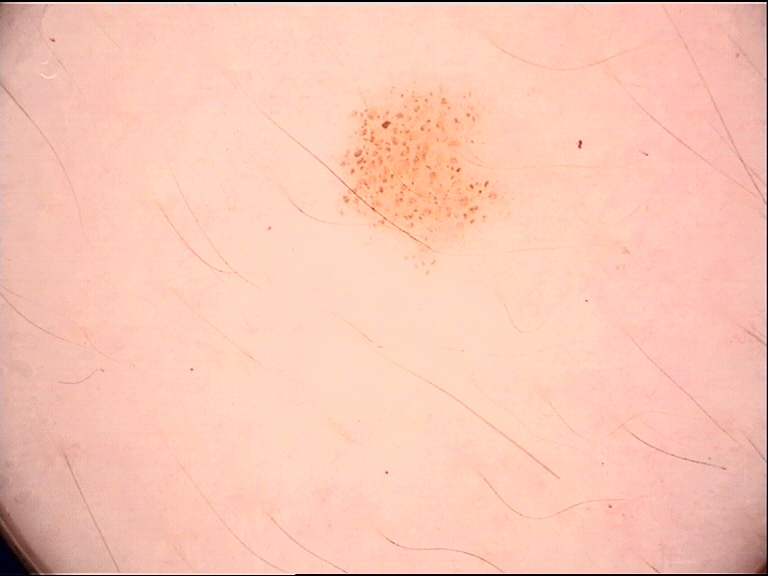diagnosis: compound nevus (expert consensus).